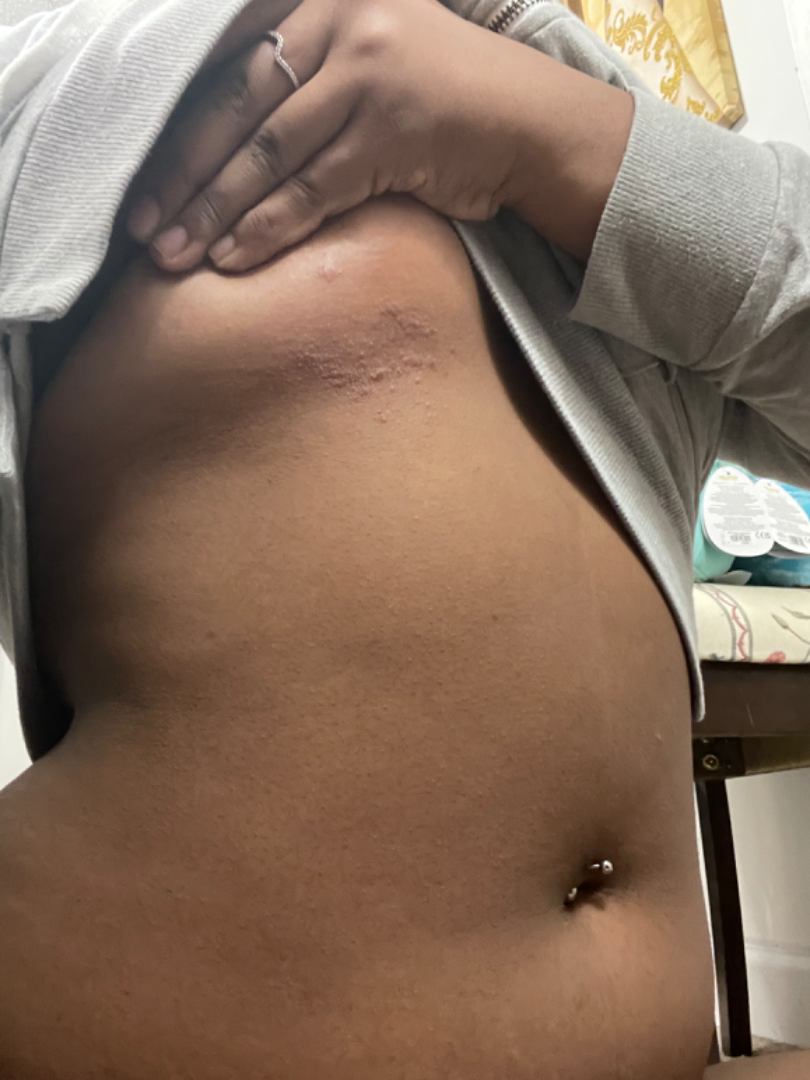affected area=front of the torso
framing=at a distance
differential diagnosis=reviewed remotely by one dermatologist: most likely Allergic Contact Dermatitis; also raised was Eczema